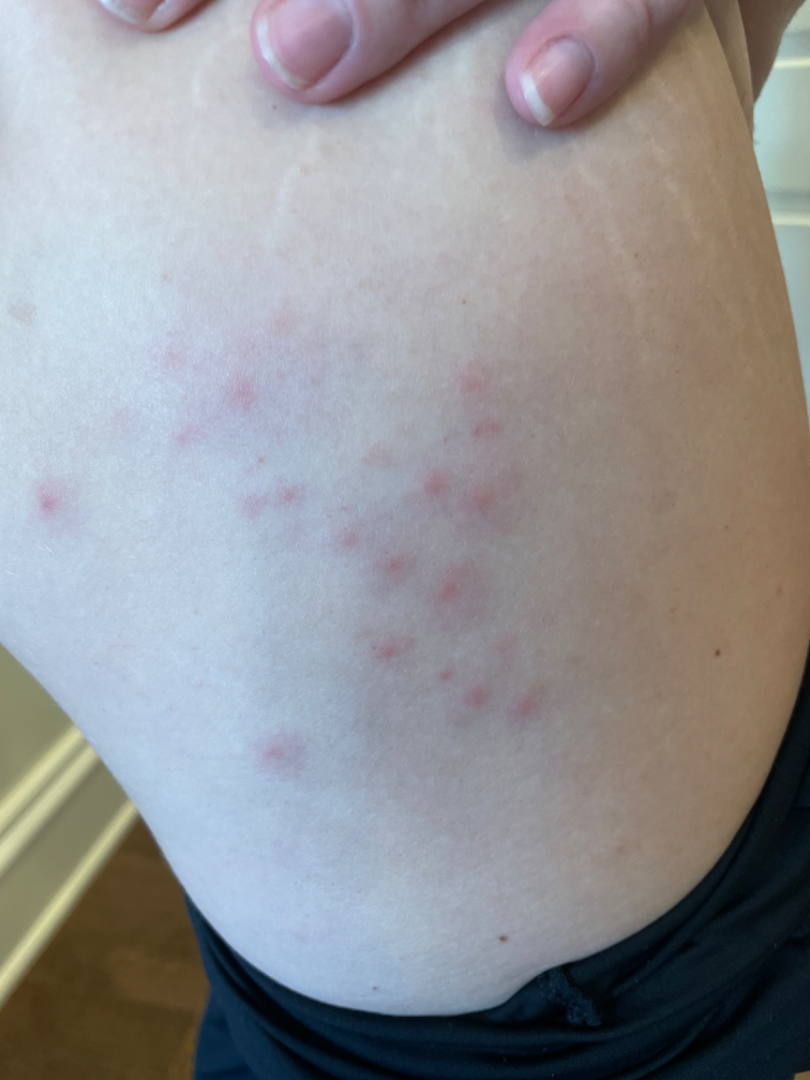assessment: could not be assessed; photo taken: close-up.